The lesion is described as raised or bumpy. An image taken at a distance. Symptoms reported: itching. Located on the arm. Self-categorized by the patient as a rash. Present for about one day — 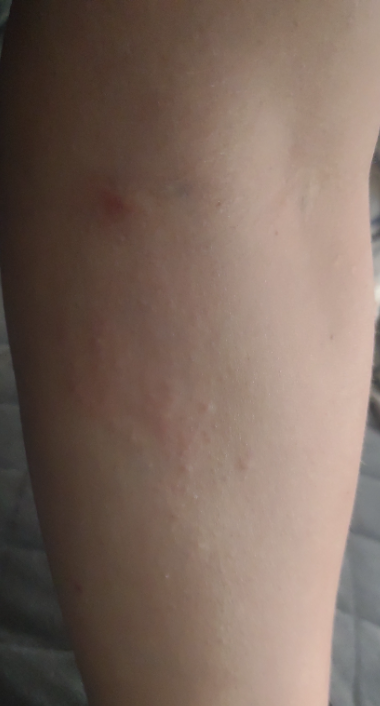{
  "assessment": "not assessable"
}